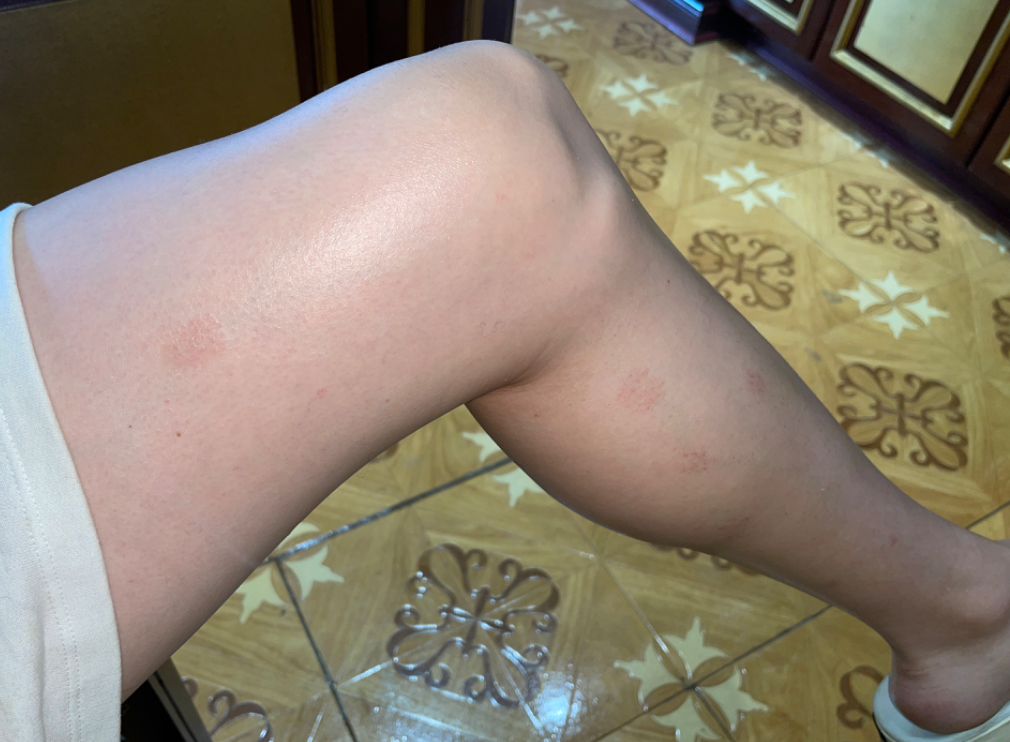anatomic site=leg | patient describes the issue as=a rash | patient-reported symptoms=bothersome appearance | view=at a distance | patient=male, age 18–29 | onset=three to twelve months | clinical impression=three dermatologists independently reviewed the case: most consistent with Eczema; less probable is Pigmented purpuric eruption.